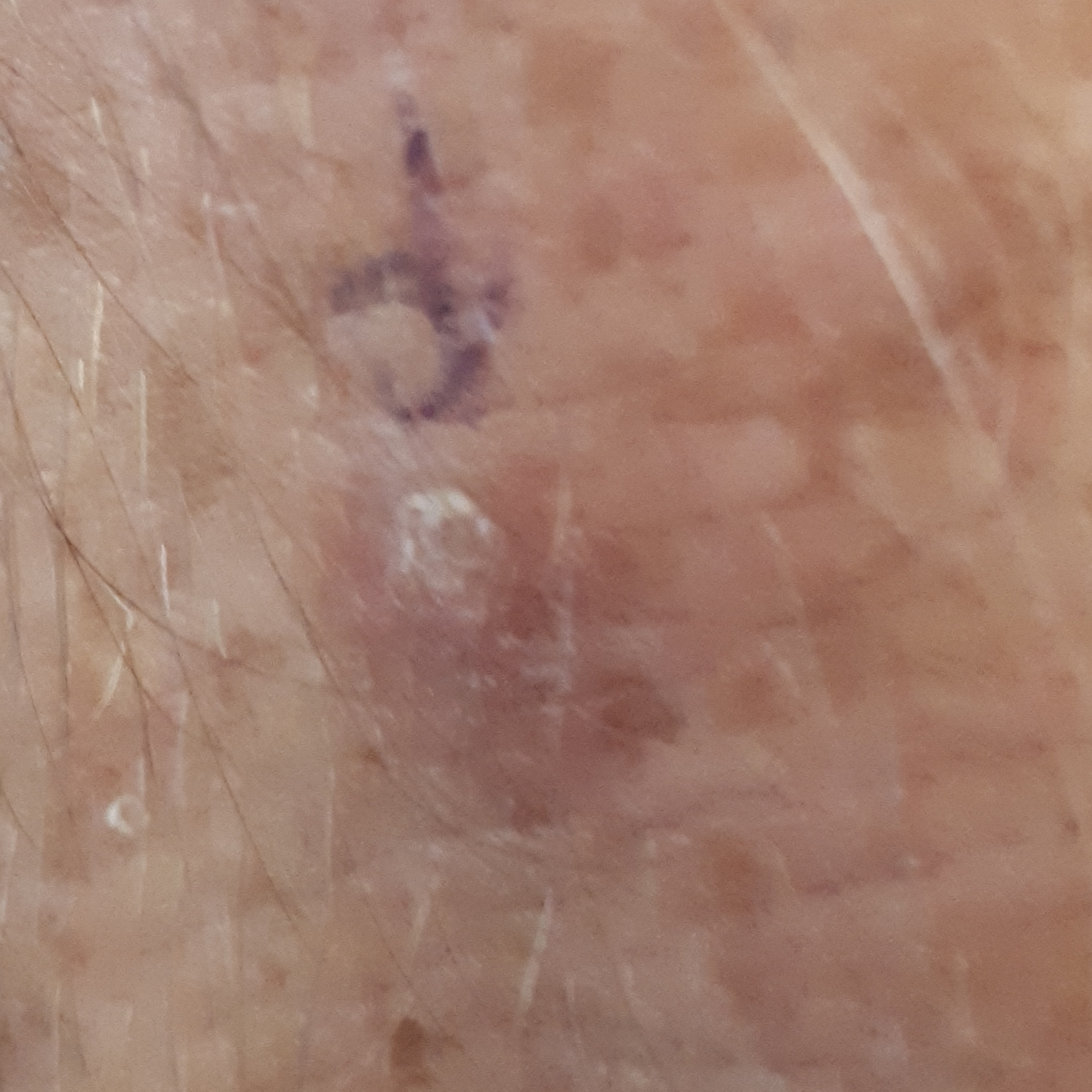Case:
– subject — age 58
– body site — an arm
– reported symptoms — none reported
– impression — actinic keratosis (clinical consensus)